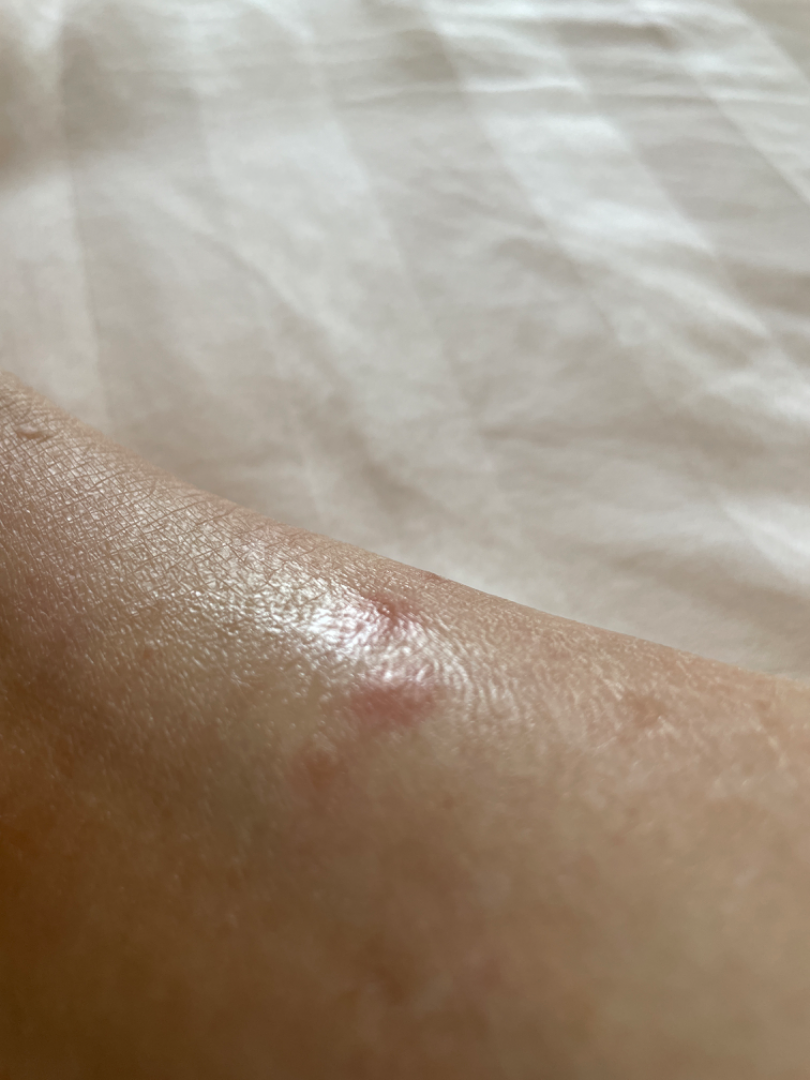Notes:
* assessment · unable to determine
* described texture · raised or bumpy
* patient · female, age 60–69
* lesion symptoms · itching
* image framing · at an angle
* symptom duration · less than one week
* patient's own categorization · a rash